A dermatoscopic image of a skin lesion: 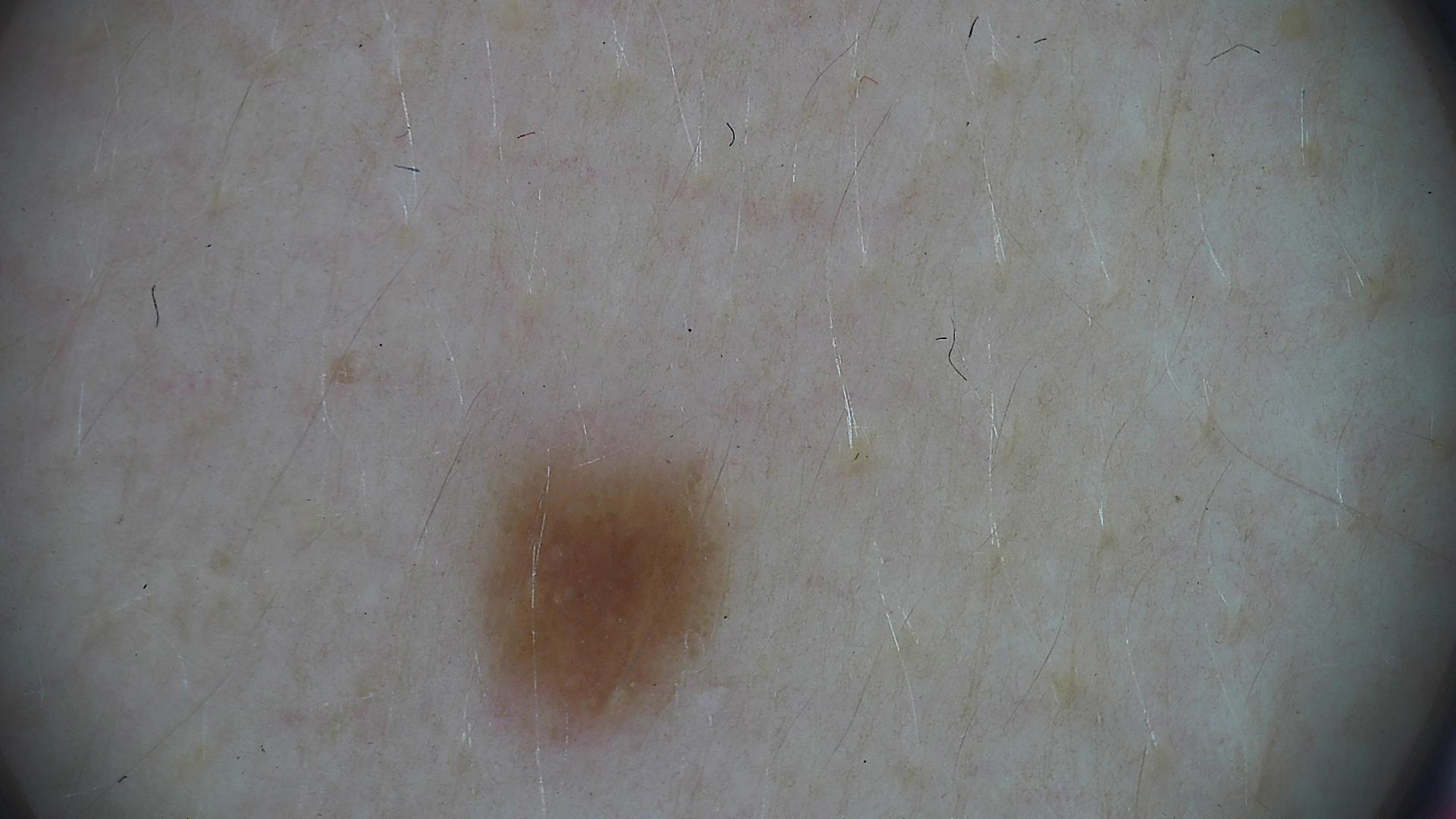Consistent with a dysplastic junctional nevus.